Dermoscopy of a skin lesion; the subject is a female in their mid-30s:
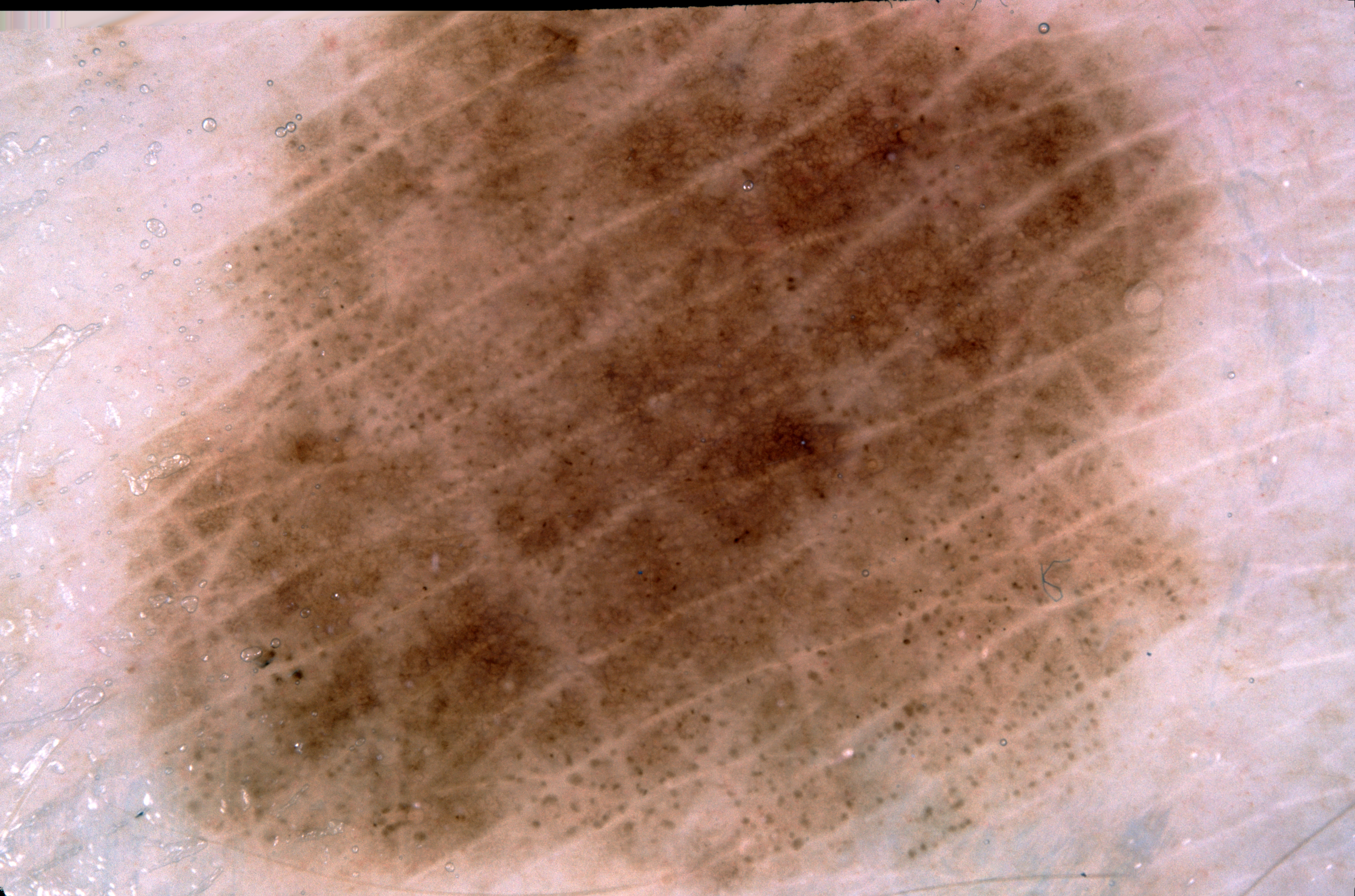Case summary:
– lesion extent · ~68% of the field
– lesion bbox · (117, 0, 1217, 895)
– dermoscopic pattern · pigment network
– lesion margin · clipped at the frame edge
– assessment · a melanoma